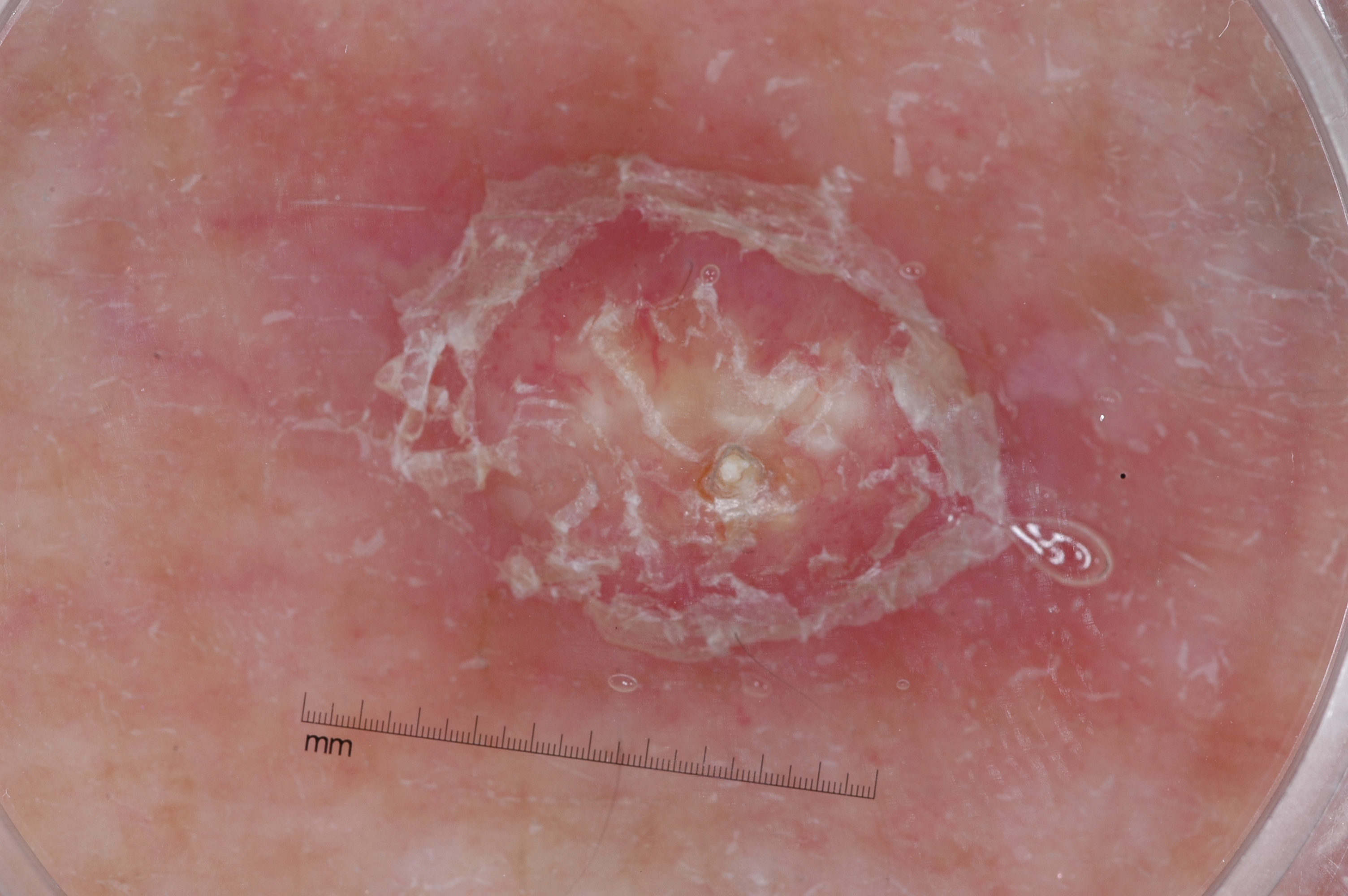| feature | finding |
|---|---|
| image type | dermoscopy of a skin lesion |
| patient | female, roughly 70 years of age |
| dermoscopic features not present | pigment network, streaks, milia-like cysts, and negative network |
| lesion size | large |
| lesion location | (181, 11, 1307, 752) |
| diagnosis | a seborrheic keratosis |